By history, prior skin cancer (patient or family), alcohol use, and pesticide exposure. A male patient in their late 50s. Recorded as FST III:
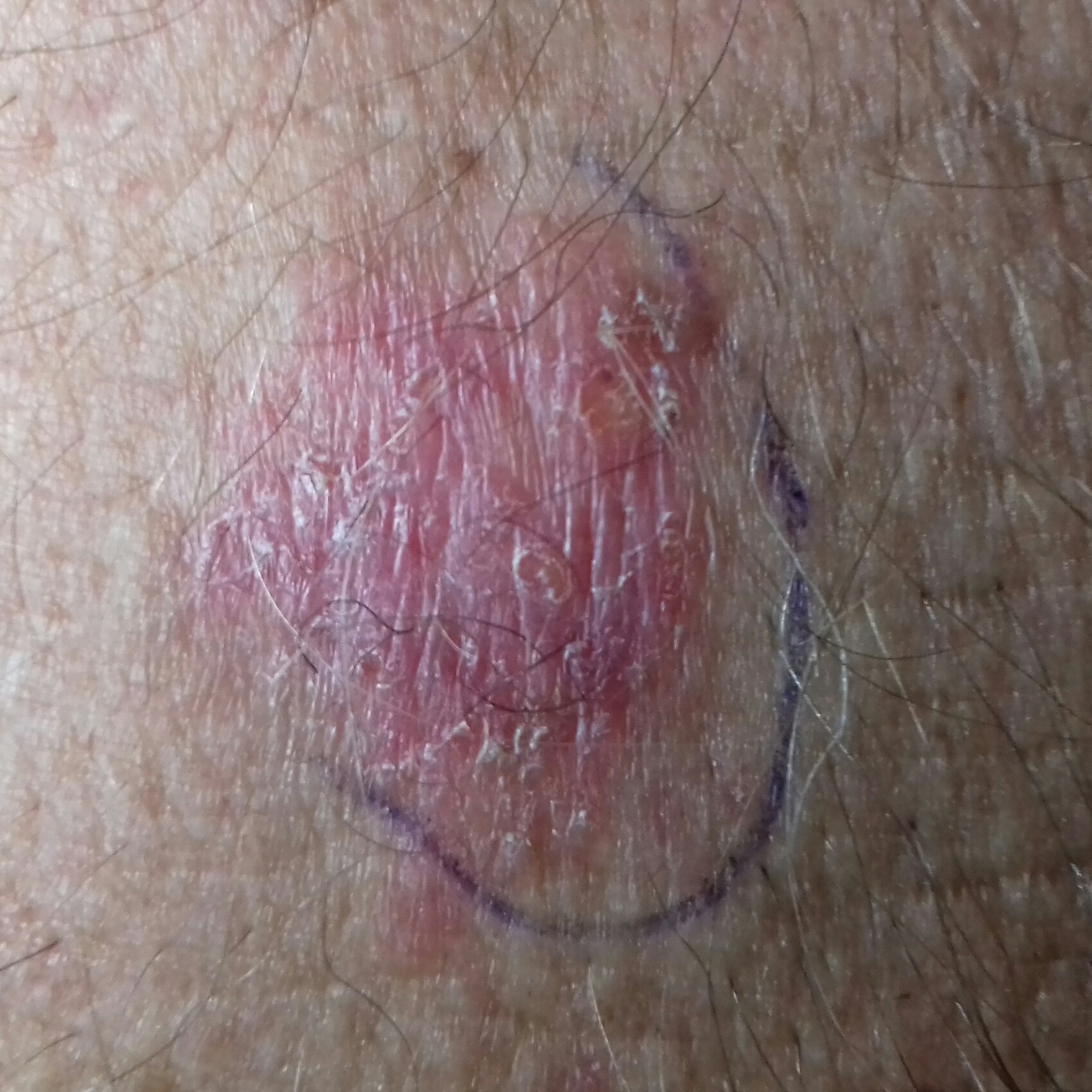Findings:
The lesion involves a forearm. Measuring about 18 × 16 mm. By the patient's account, the lesion itches and has grown.
Conclusion:
The biopsy diagnosis was a skin cancer — a squamous cell carcinoma.